Located on the back of the torso. Male contributor, age 18–29. The photo was captured at an angle: 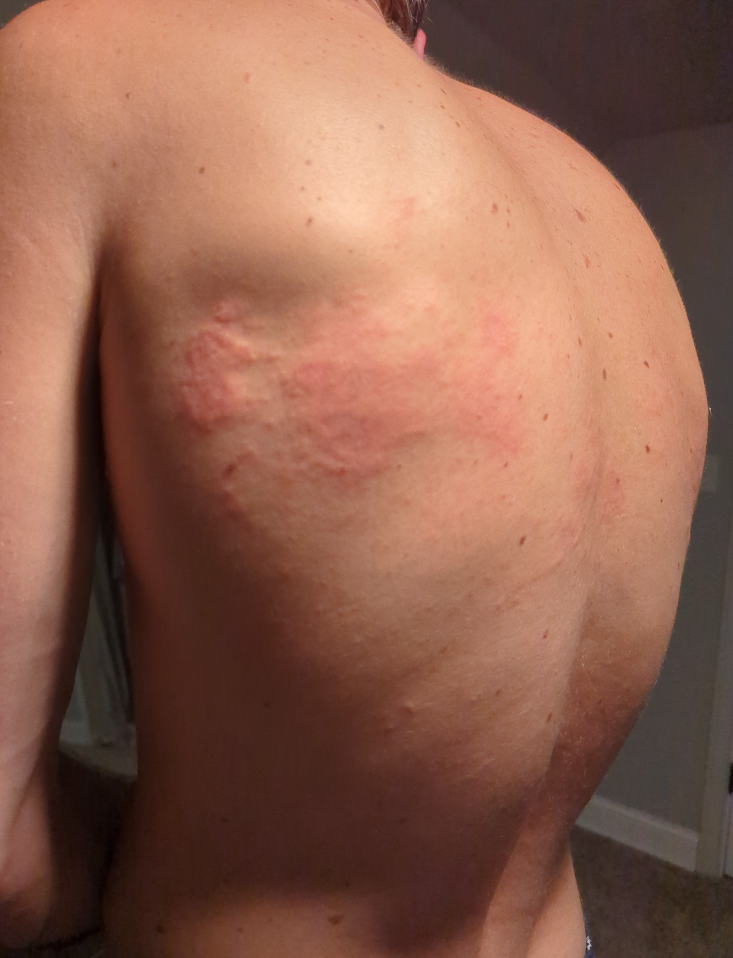| feature | finding |
|---|---|
| present for | one to four weeks |
| lesion symptoms | enlargement and itching |
| skin tone | Fitzpatrick II; lay graders estimated MST 2 (US pool) or 4 (India pool) |
| lesion texture | raised or bumpy |
| self-categorized as | a rash |
| differential diagnosis | consistent with Urticaria |